A dermoscopic view of a skin lesion. A female subject aged 13-17 — 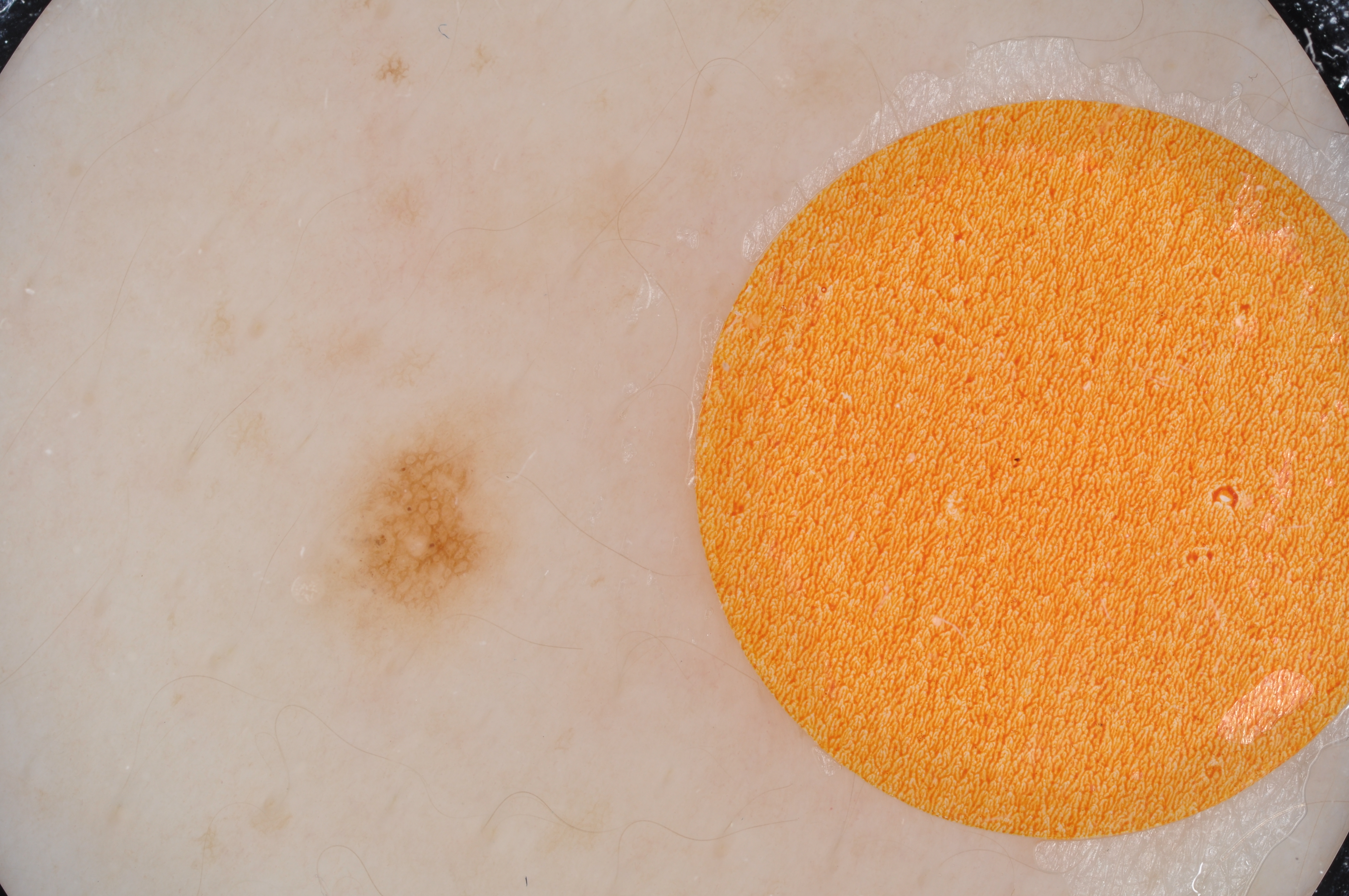{"dermoscopic_features": {"present": ["pigment network"], "absent": ["negative network", "globules", "streaks", "milia-like cysts"]}, "lesion_location": {"bbox_xyxy": [302, 378, 537, 679]}, "lesion_extent": {"approx_field_fraction_pct": 4}, "diagnosis": {"name": "melanocytic nevus", "malignancy": "benign", "lineage": "melanocytic", "provenance": "clinical"}}